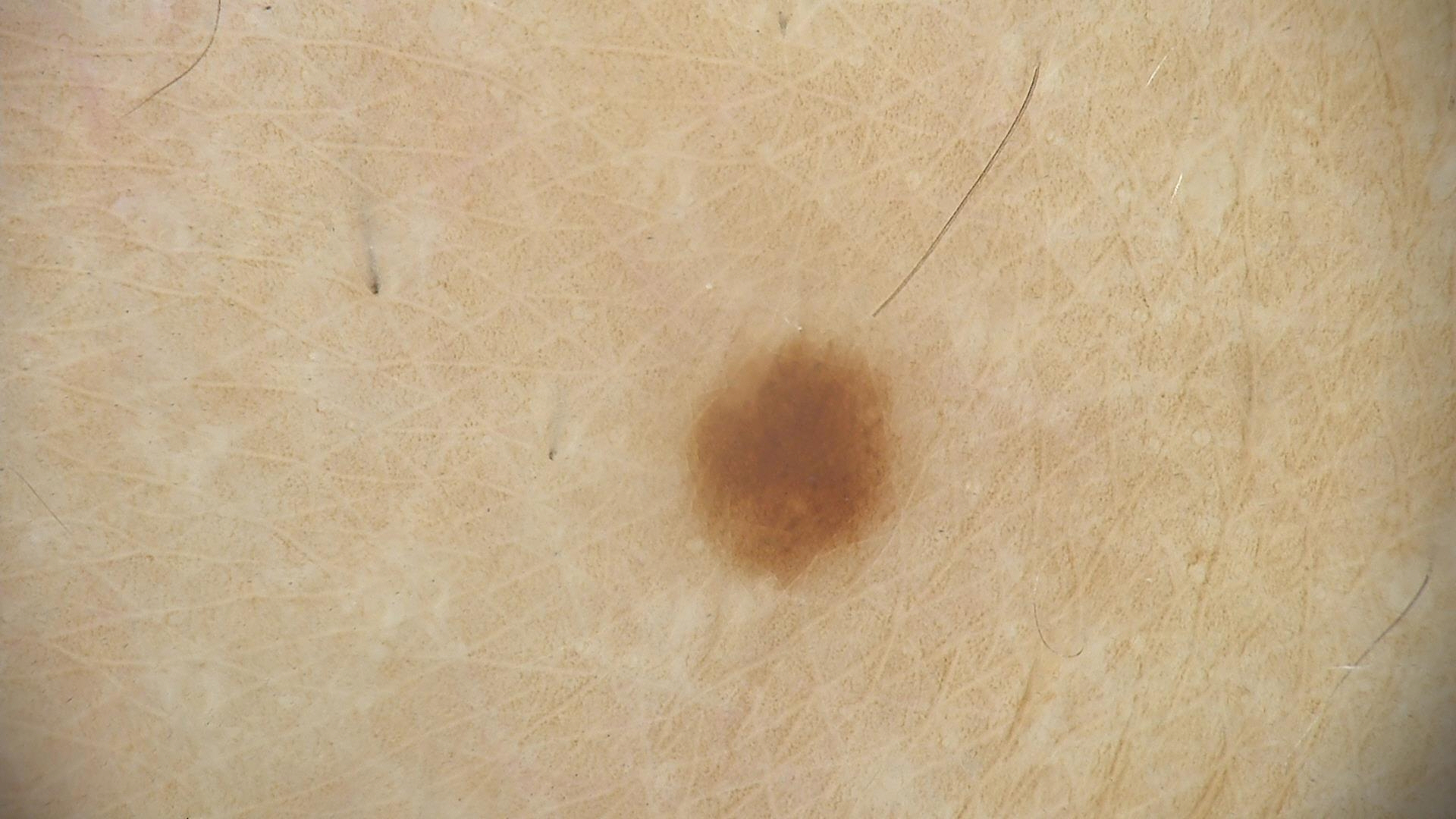diagnostic label: dysplastic junctional nevus (expert consensus).